A dermatoscopic image of a skin lesion; acquired for a research image collection, with no referral diagnosis; a female subject 71 years of age:
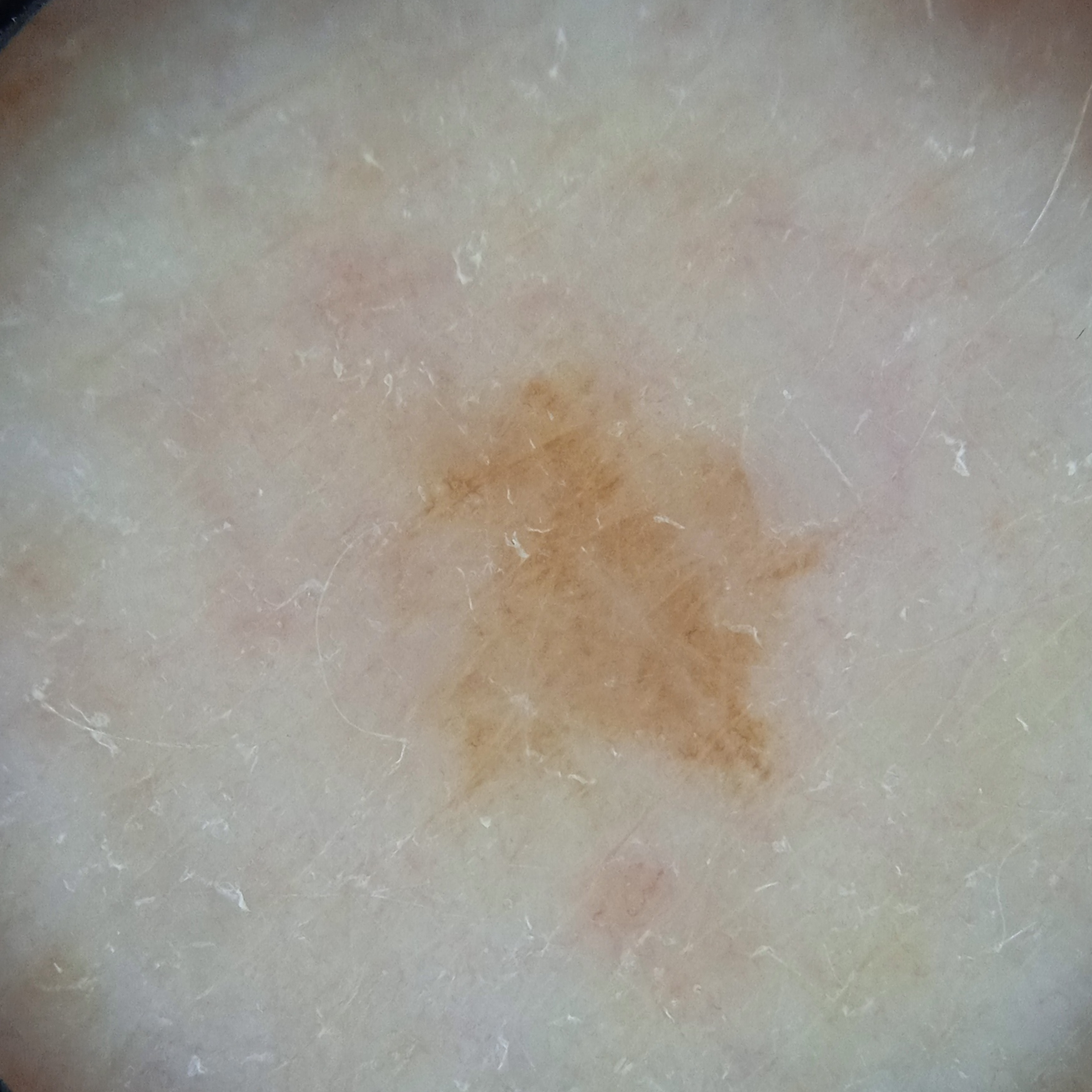Located on an arm. Measuring roughly 6.1 mm. Four dermatologists reviewed the lesion; the consensus was a melanocytic nevus; diagnostic confidence was moderate.